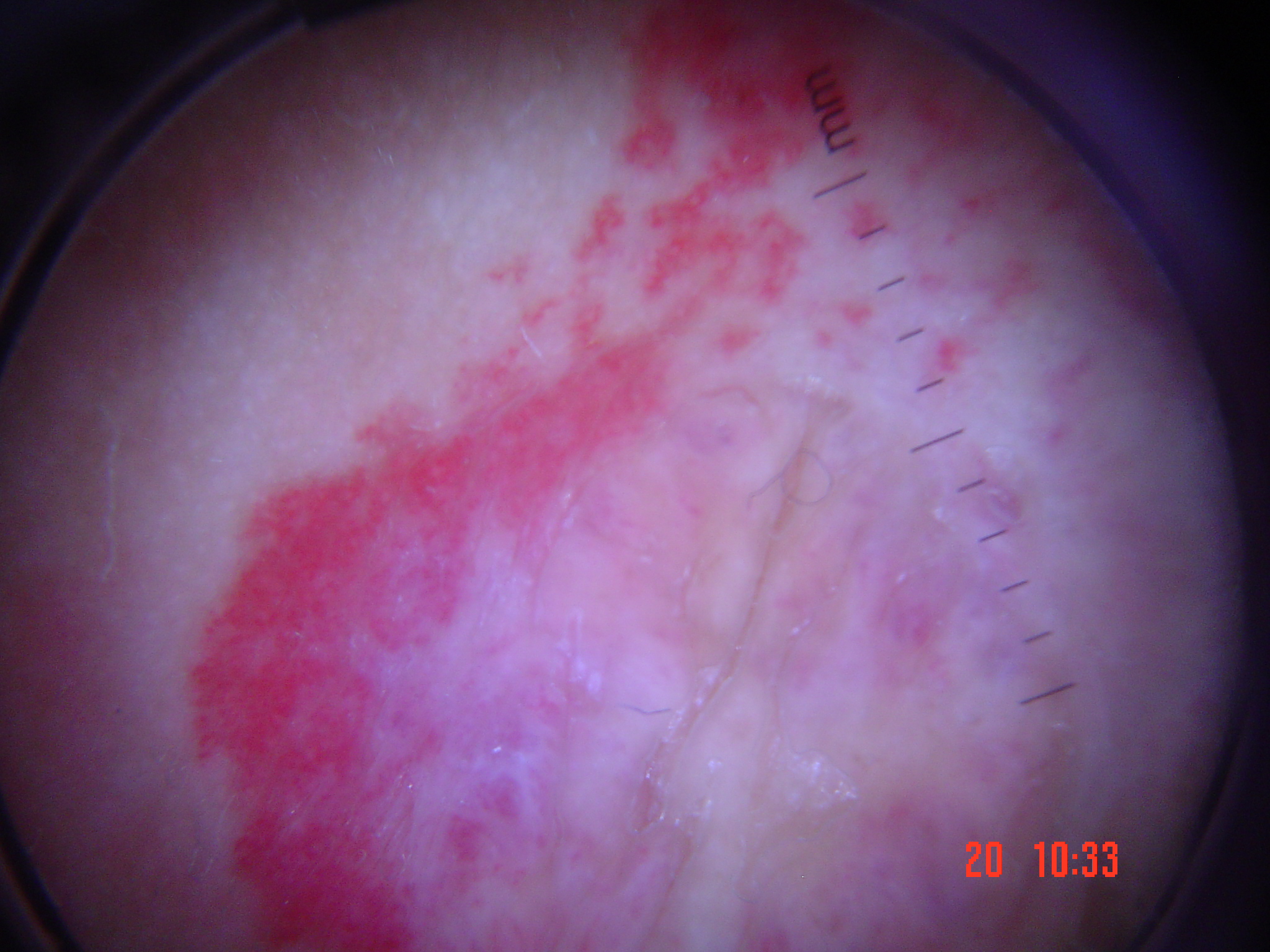diagnostic label: hemangioma (expert consensus).